A dermoscopic photograph of a skin lesion:
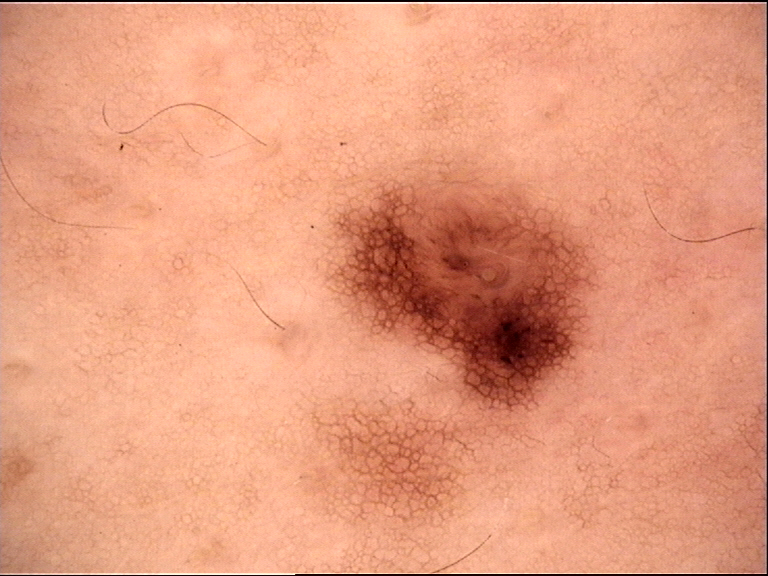subtype: banal; diagnosis: junctional nevus (expert consensus).